The contributor reports the lesion is raised or bumpy. The condition has been present for about one day. Self-categorized by the patient as skin that appeared healthy to them. The affected area is the arm. This image was taken at a distance. Fitzpatrick skin type IV. The contributor reports itching.
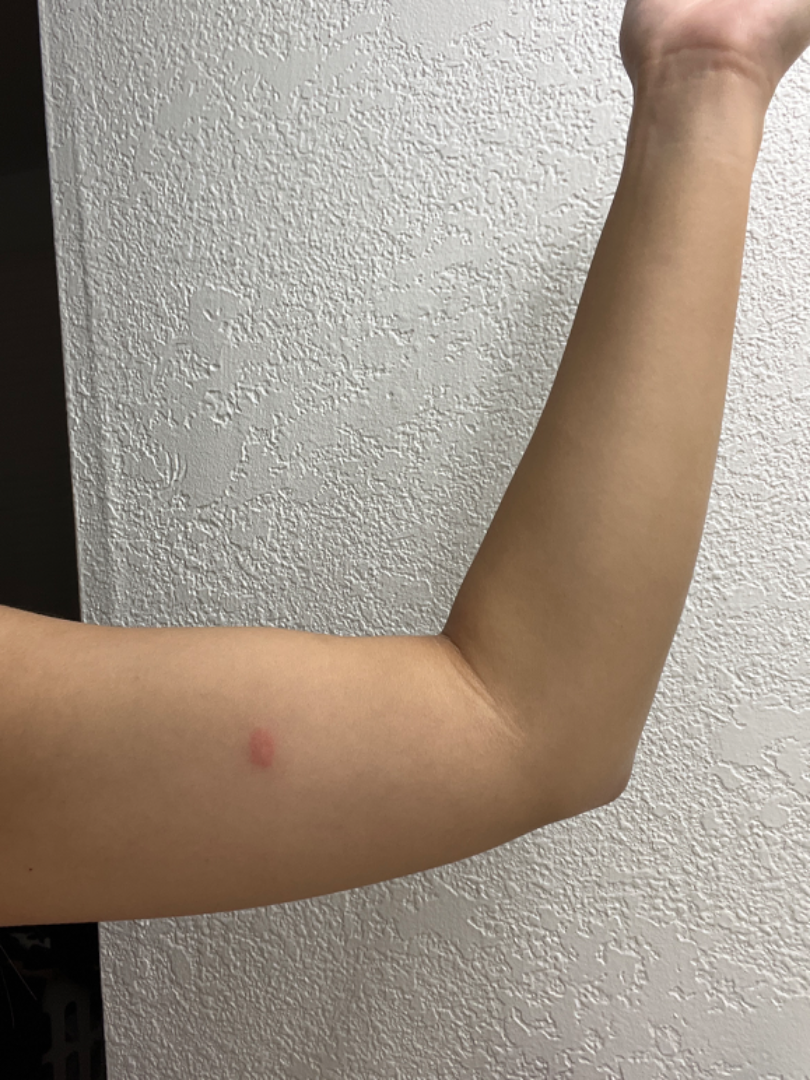differential diagnosis=Insect Bite and Mastocytoma were each considered, in no particular order.